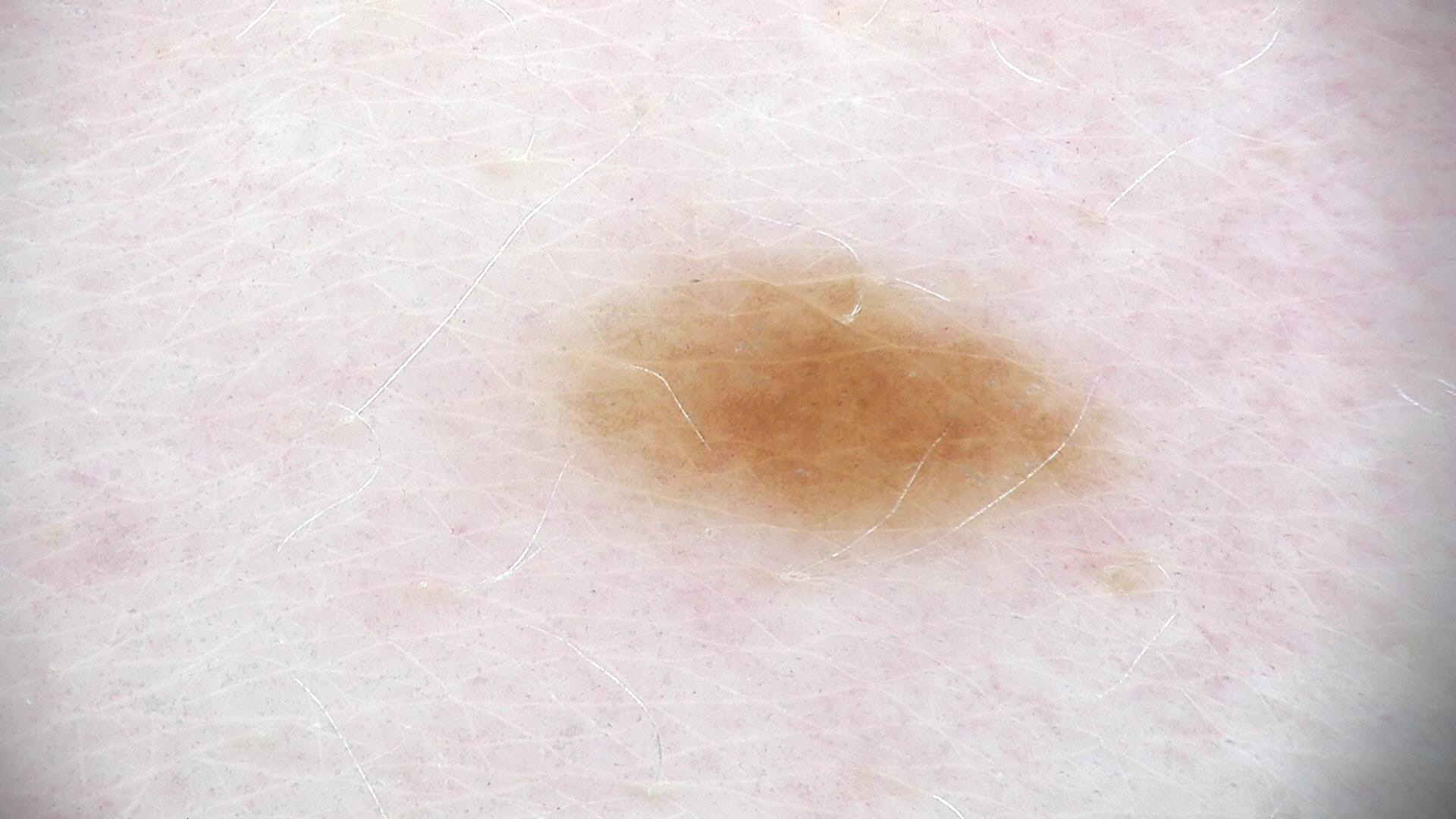Findings:
• label · dysplastic junctional nevus (expert consensus)